The photo was captured at a distance. The subject is male. The affected area is the head or neck:
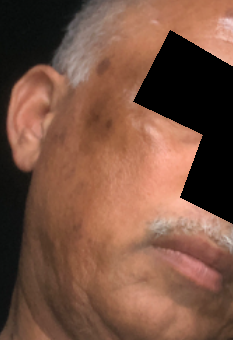On independent review by the dermatologists, Prurigo nodularis (0.50); Cutaneous lupus (0.50).